A male patient aged 73-77 · an overview clinical photograph of a skin lesion · the patient is skin type II: 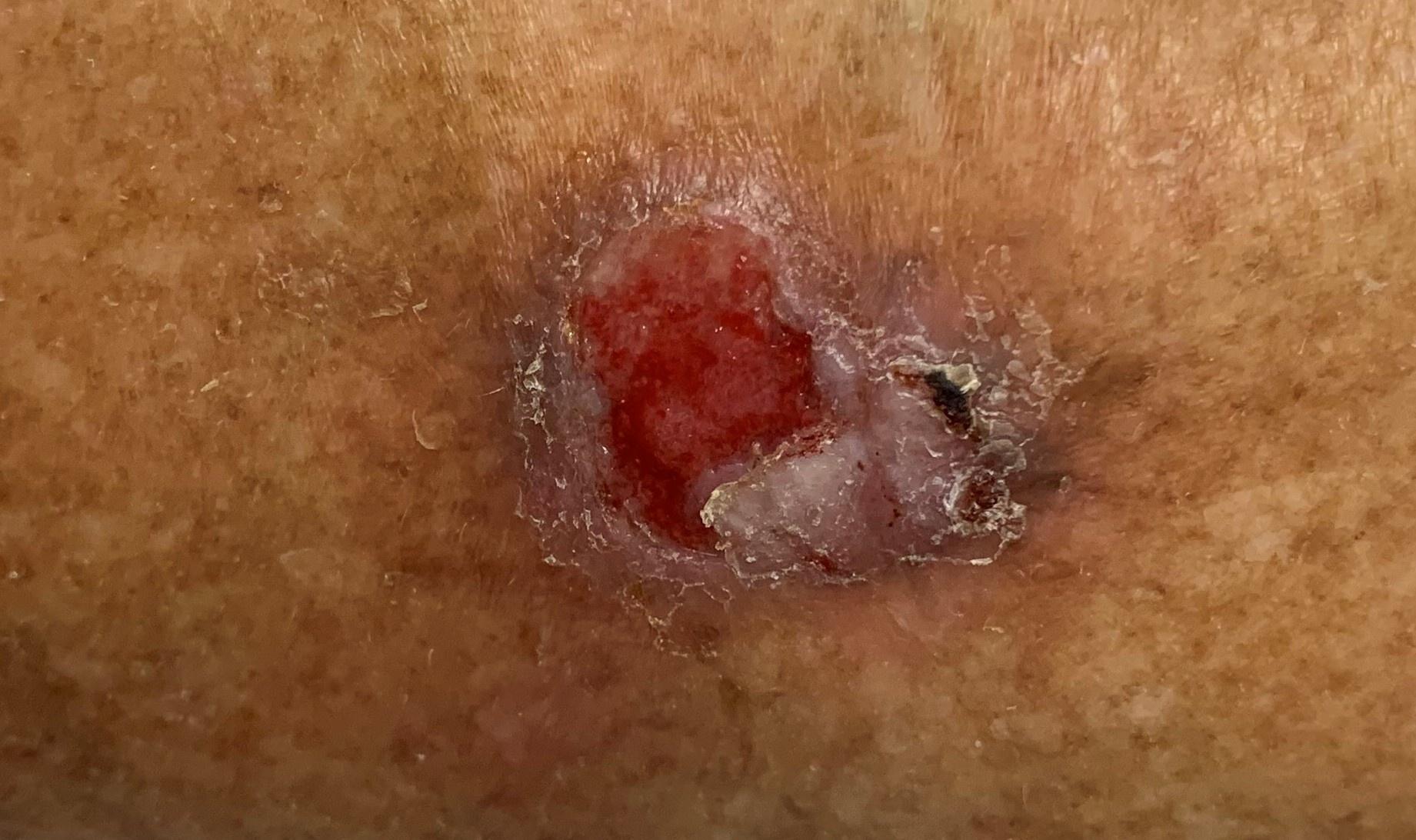{
  "lesion_location": {
    "region": "a lower extremity"
  },
  "diagnosis": {
    "name": "Basal cell carcinoma",
    "malignancy": "malignant",
    "confirmation": "histopathology",
    "lineage": "adnexal"
  }
}